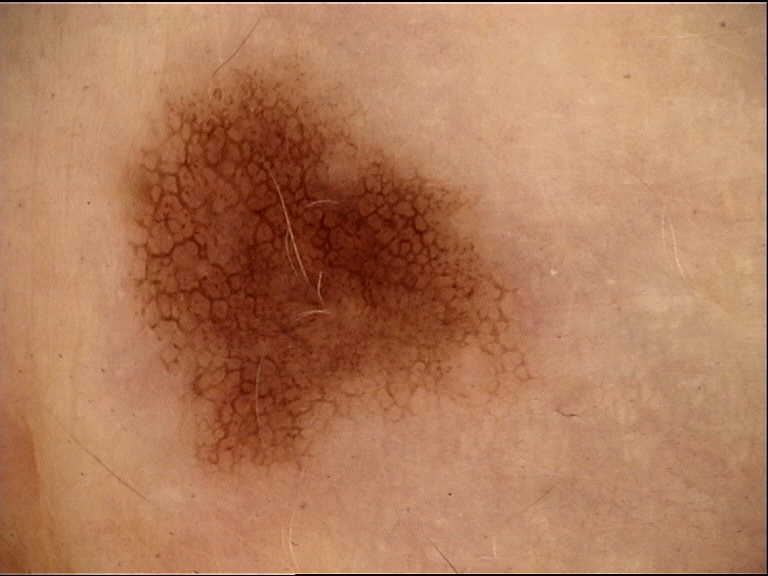Impression:
The diagnostic label was a benign lesion — a dysplastic junctional nevus.